Fitzpatrick phototype II · a male subject aged 78-82 · a contact-polarized dermoscopy image of a skin lesion — 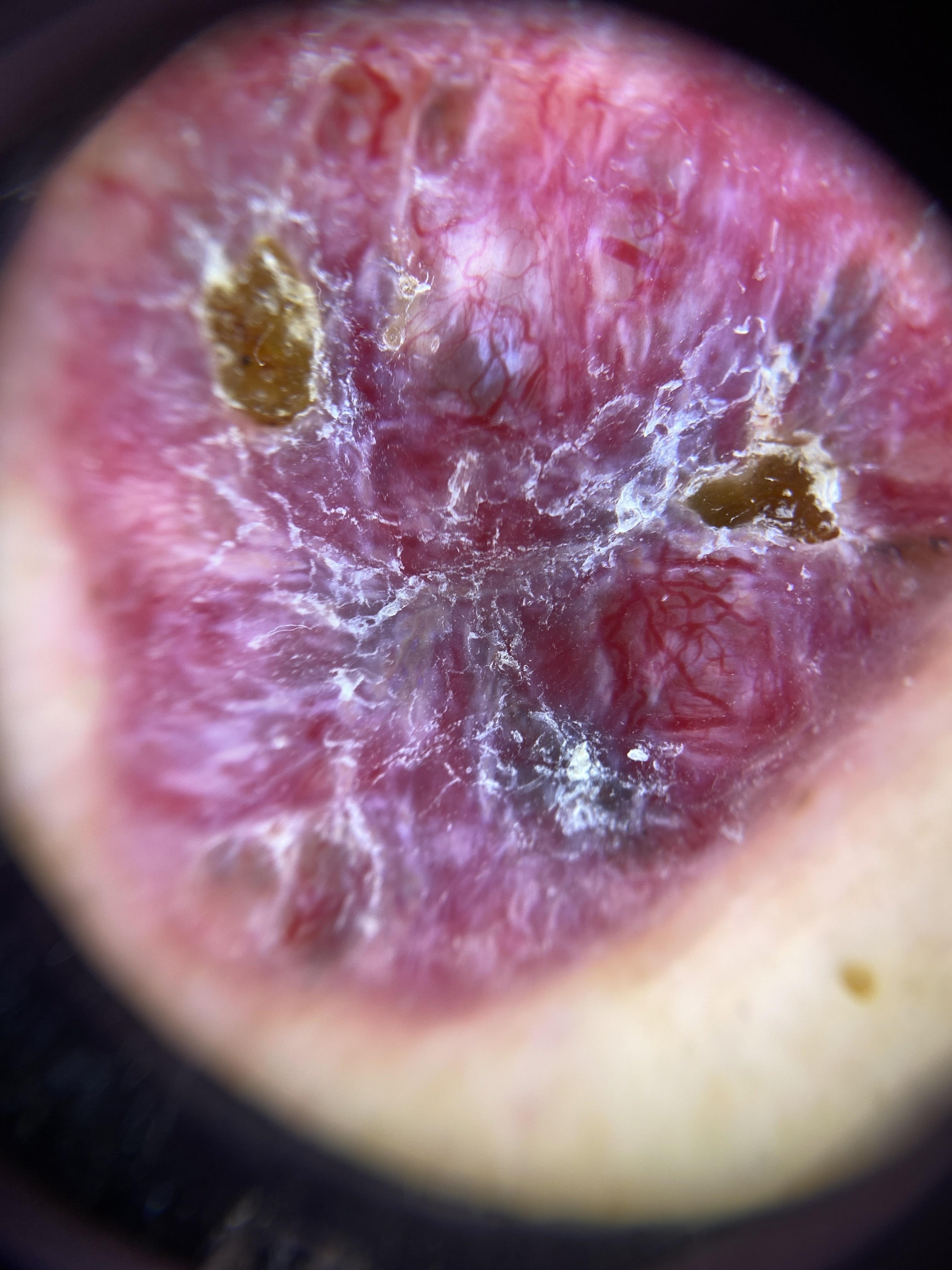Image and clinical context:
The lesion is located on the posterior trunk.
Diagnosis:
Confirmed on histopathology as a malignancy — a basal cell carcinoma.